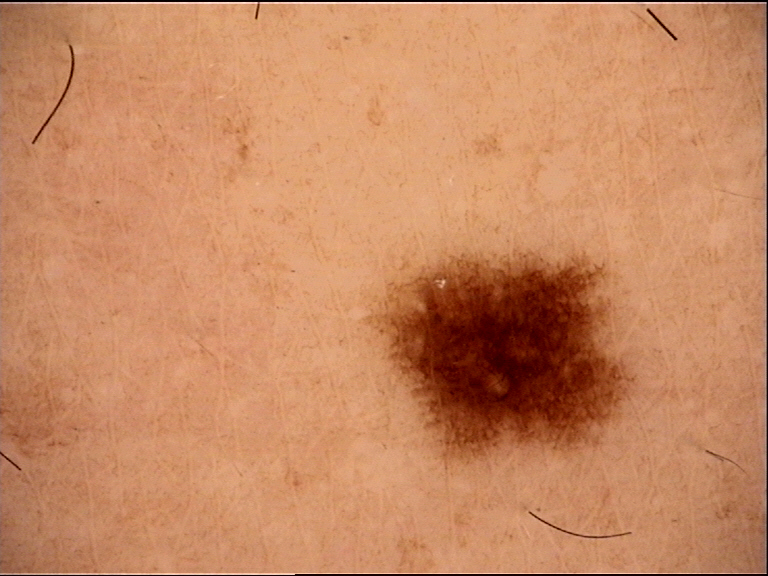Case:
• imaging · dermatoscopy
• lesion type · banal
• assessment · junctional nevus (expert consensus)